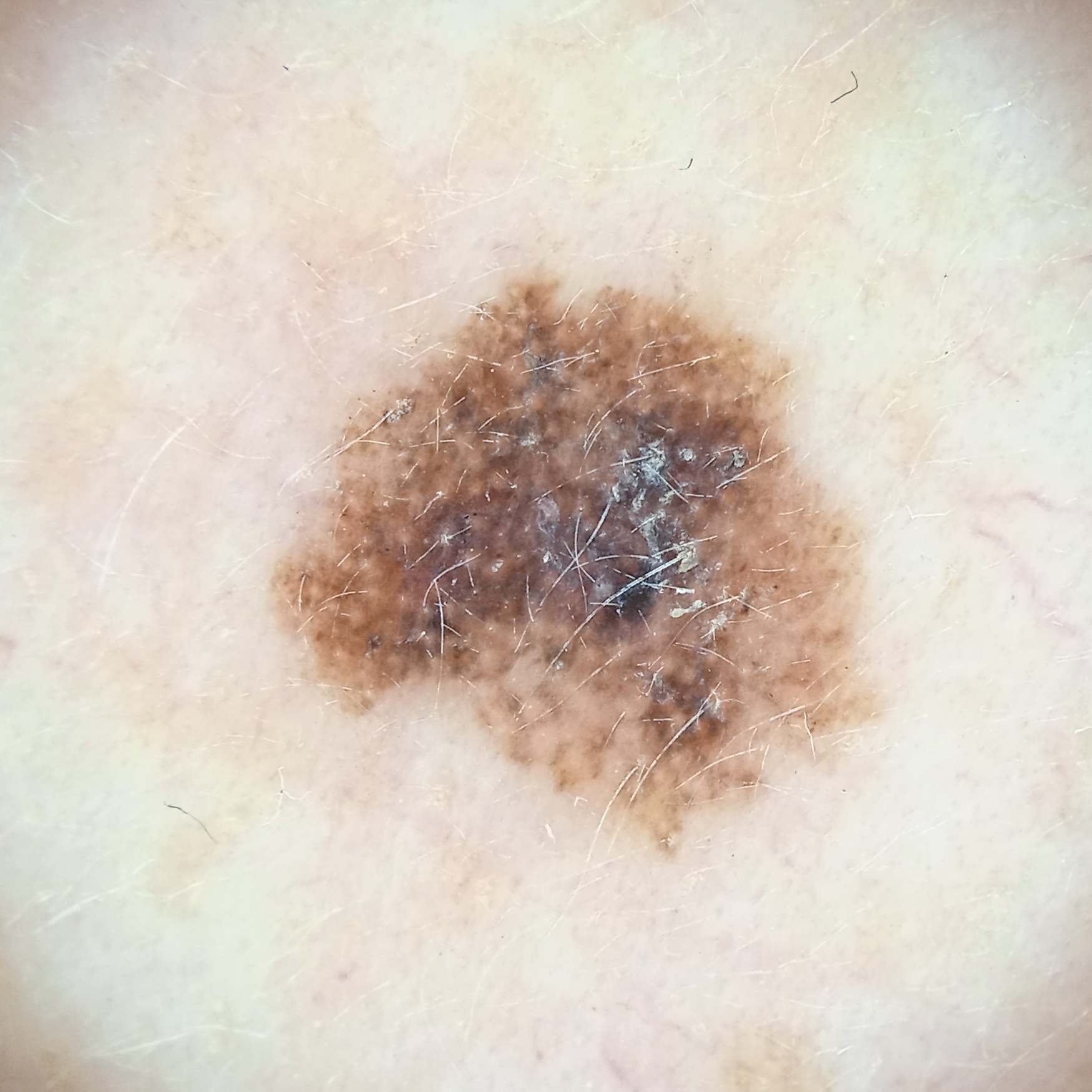  sun_reaction: skin reddens with sun exposure
  image: dermoscopy
  referral: clinical suspicion of melanoma
  patient:
    age: 50
    sex: female
  risk_factors:
    positive:
      - a personal history of skin cancer
  lesion_location: the face
  lesion_size:
    diameter_mm: 7.0
  diagnosis:
    name: melanoma
    malignancy: malignant
    procedure: excision
    tumor_thickness_mm: 0.4